A skin lesion imaged with a dermatoscope. A moderate number of moles by the patient's own estimate. By self-report, no personal history of skin cancer. Collected as part of a research study, without a referral diagnosis:
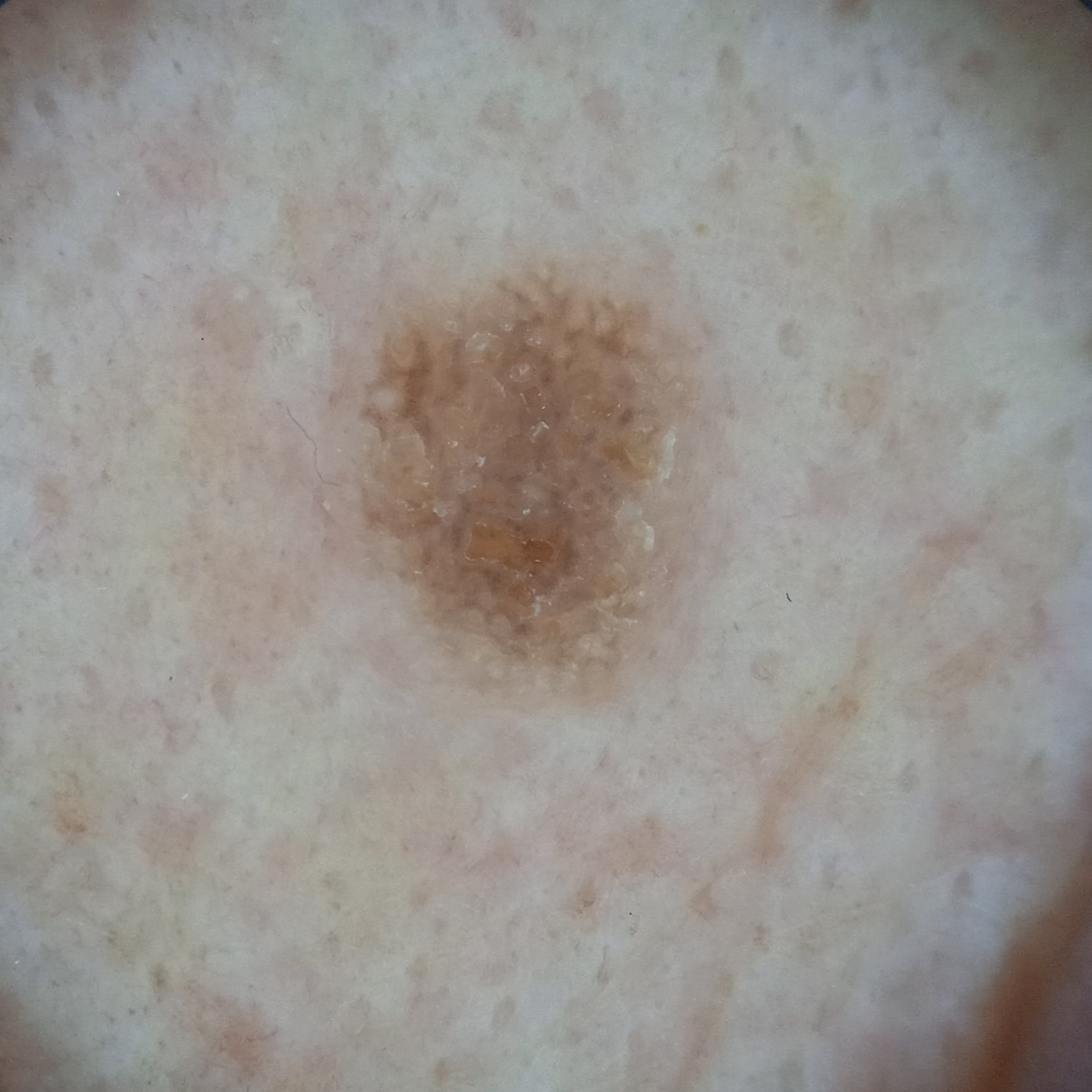Conclusion:
The dermatologists' assessment was a seborrheic keratosis.